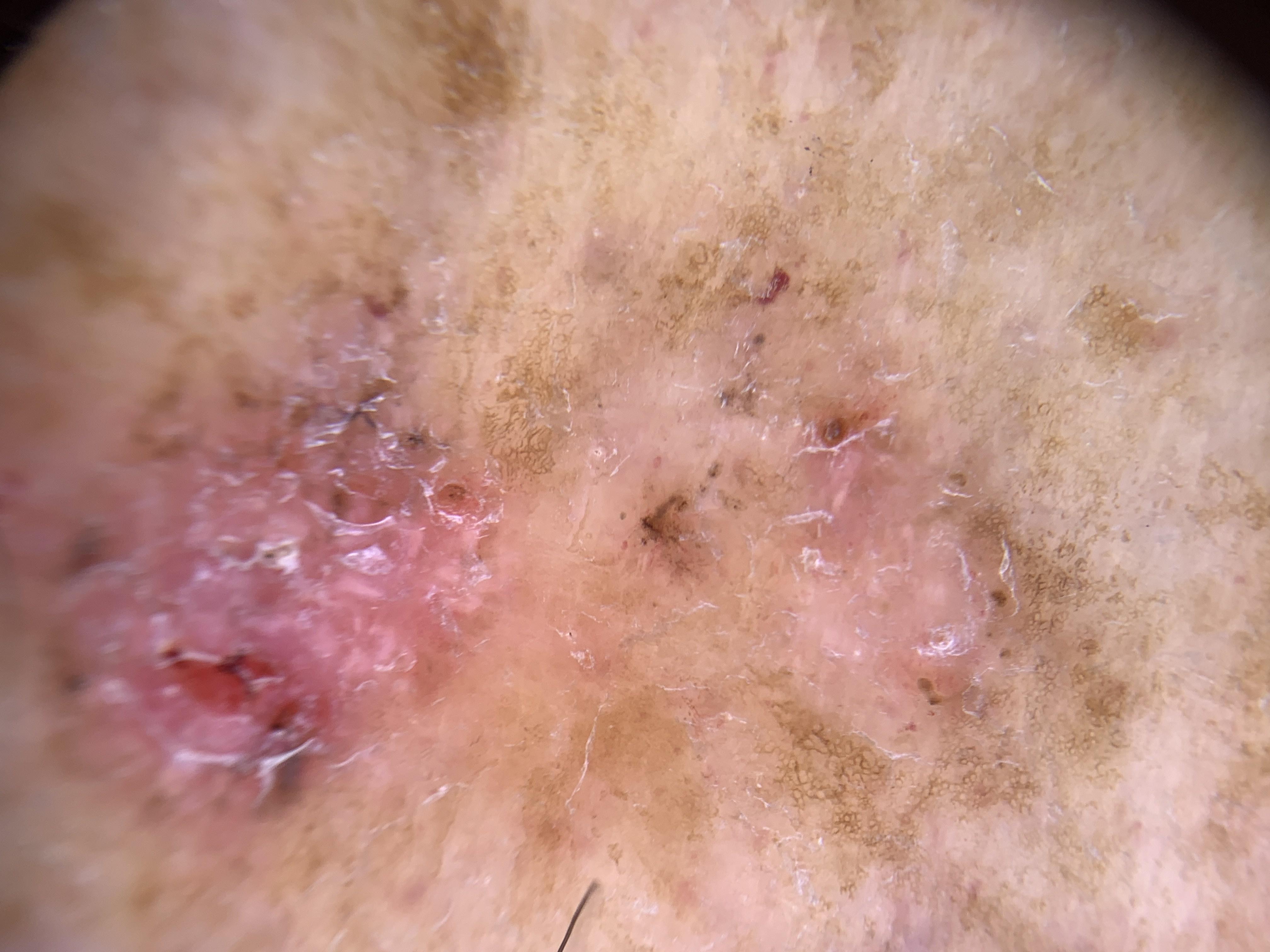The patient is Fitzpatrick skin type II.
A contact-polarized dermoscopy image of a skin lesion.
The chart notes a previous melanoma.
Biopsy-confirmed as an adnexal lesion — a basal cell carcinoma.